An image taken at an angle:
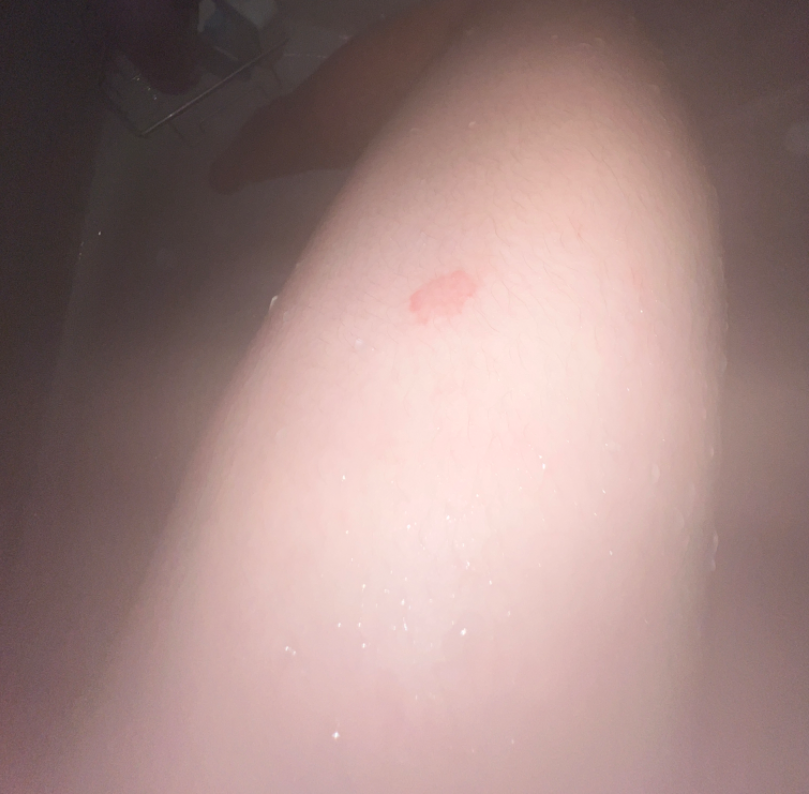Tinea (weight 0.33); Eczema (weight 0.33); Pityriasis rosea (weight 0.33).